Acquired for a research image collection, with no referral diagnosis — 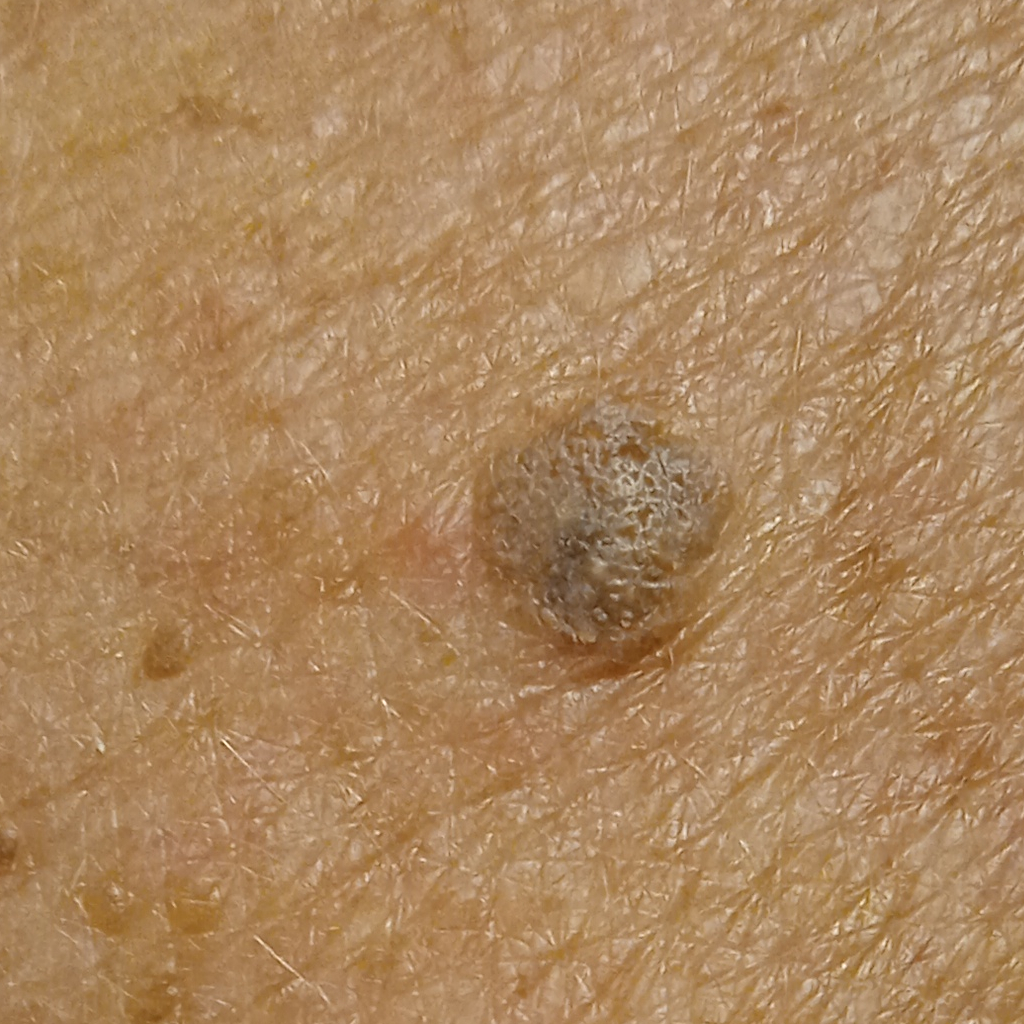Q: What is the anatomic site?
A: the back
Q: How large is the lesion?
A: 7.3 mm
Q: What was the diagnosis?
A: seborrheic keratosis (dermatologist consensus)